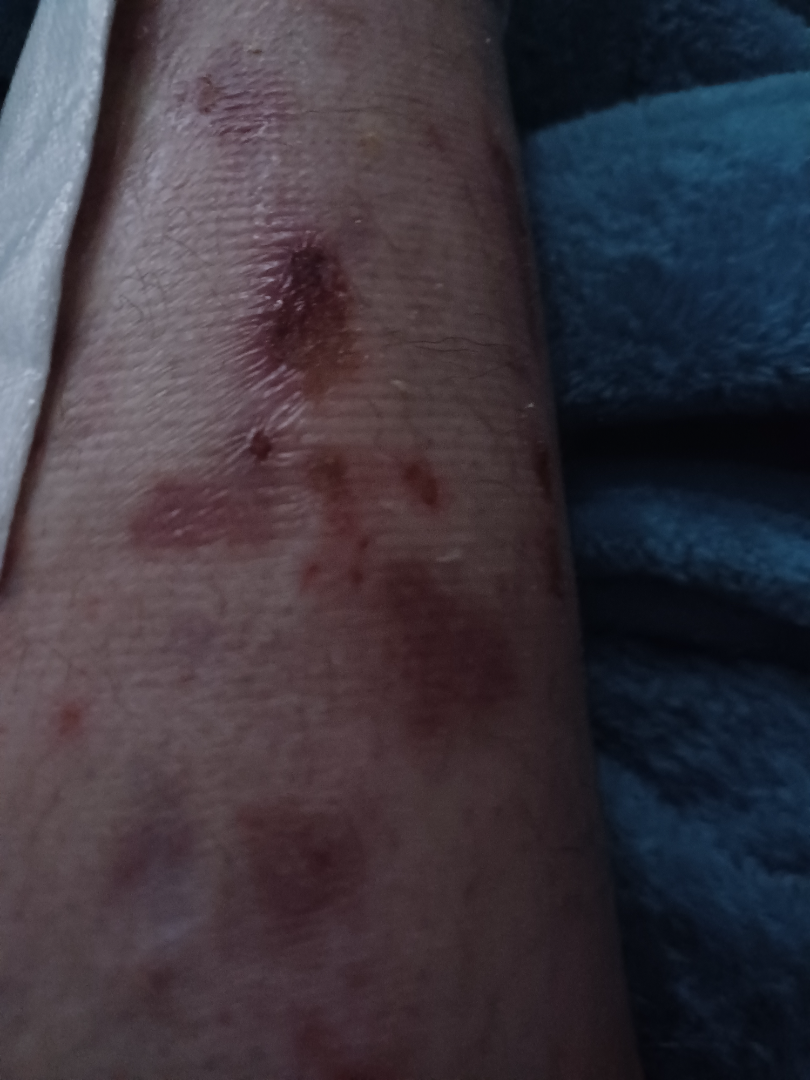Case summary:
– dermatologist impression · three independent reviewers: the differential includes Abrasion, scrape, or scab and Bullous Pemphigoid, with no clear leading consideration; less probable is ecchymoses; less likely is Eczema